A dermoscopy image of a single skin lesion.
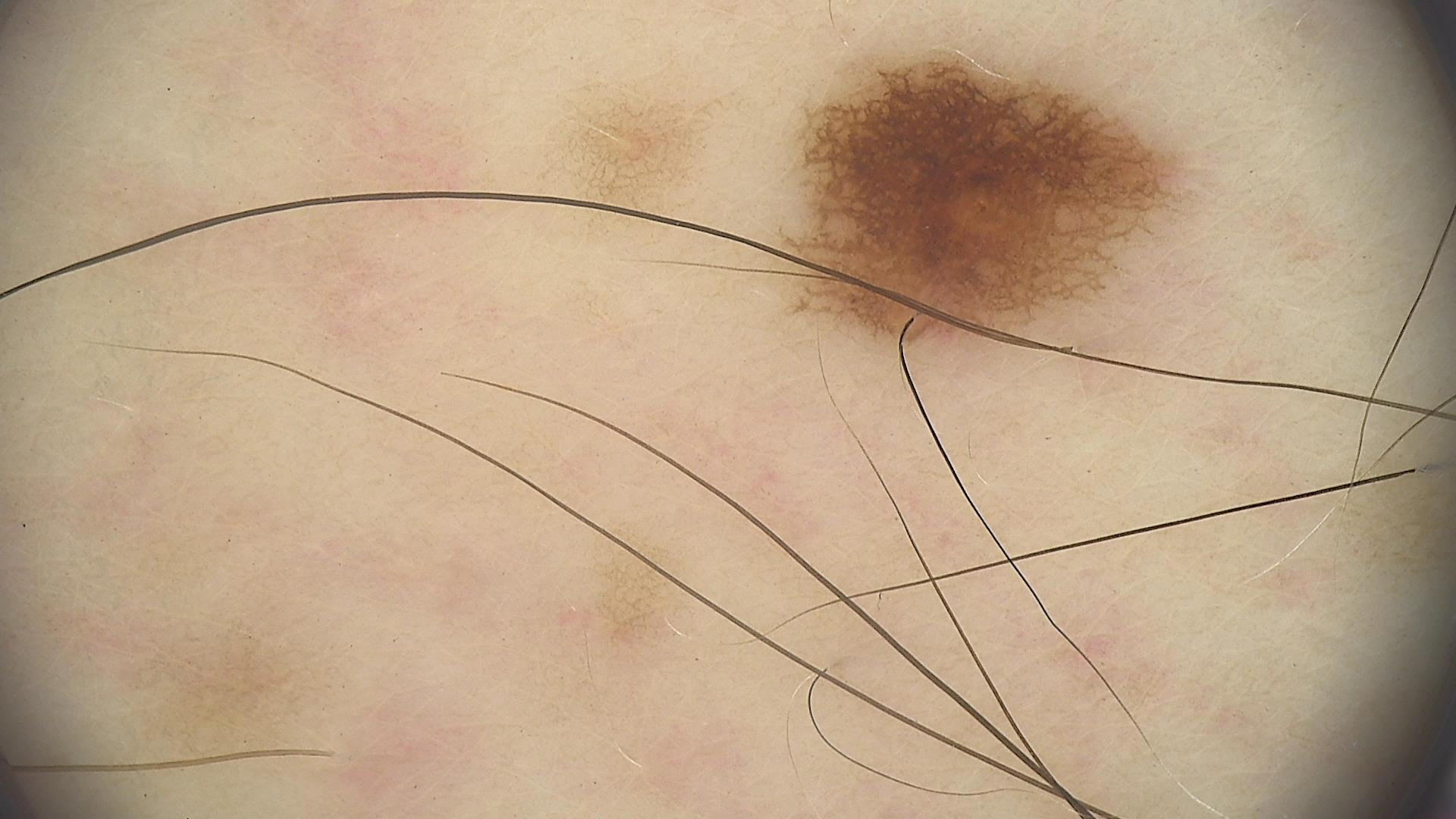The diagnosis was a dysplastic junctional nevus.